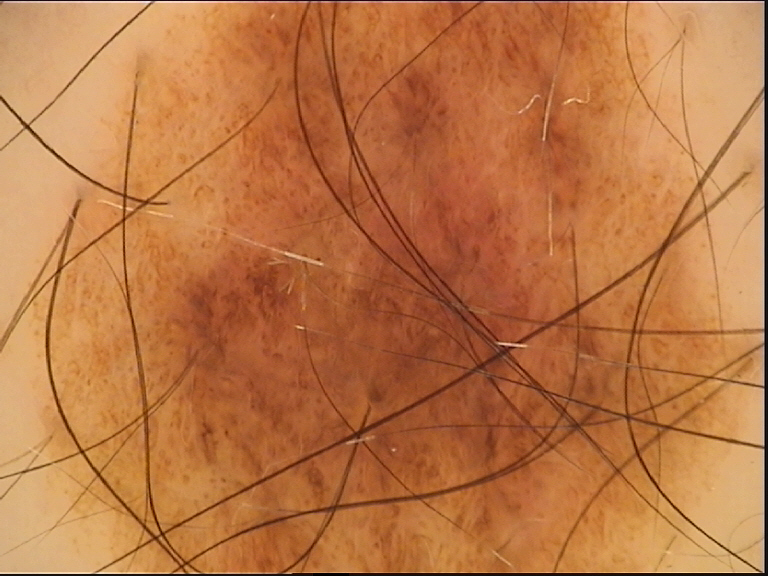Classified as a dysplastic junctional nevus.